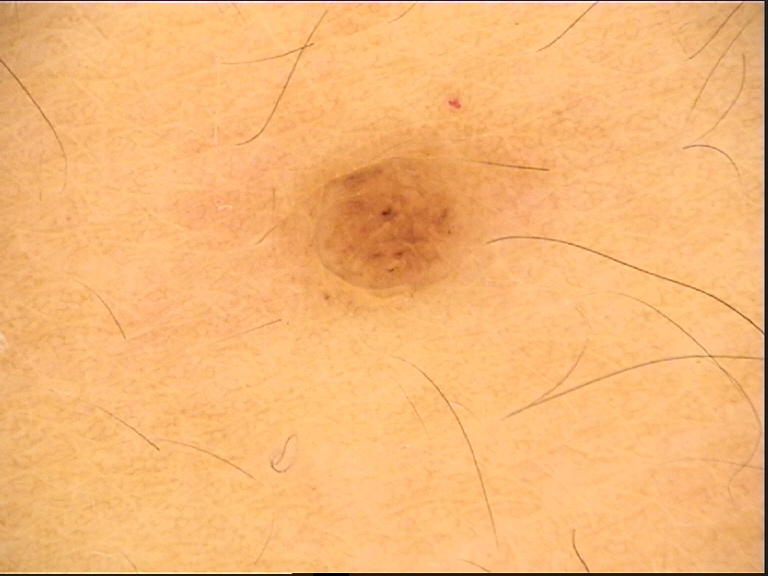<case>
  <lesion_type>
    <main_class>banal</main_class>
    <pattern>compound</pattern>
  </lesion_type>
  <diagnosis>
    <name>compound nevus</name>
    <code>cb</code>
    <malignancy>benign</malignancy>
    <super_class>melanocytic</super_class>
    <confirmation>expert consensus</confirmation>
  </diagnosis>
</case>